This image was taken at an angle · the leg is involved · male patient, age 18–29: 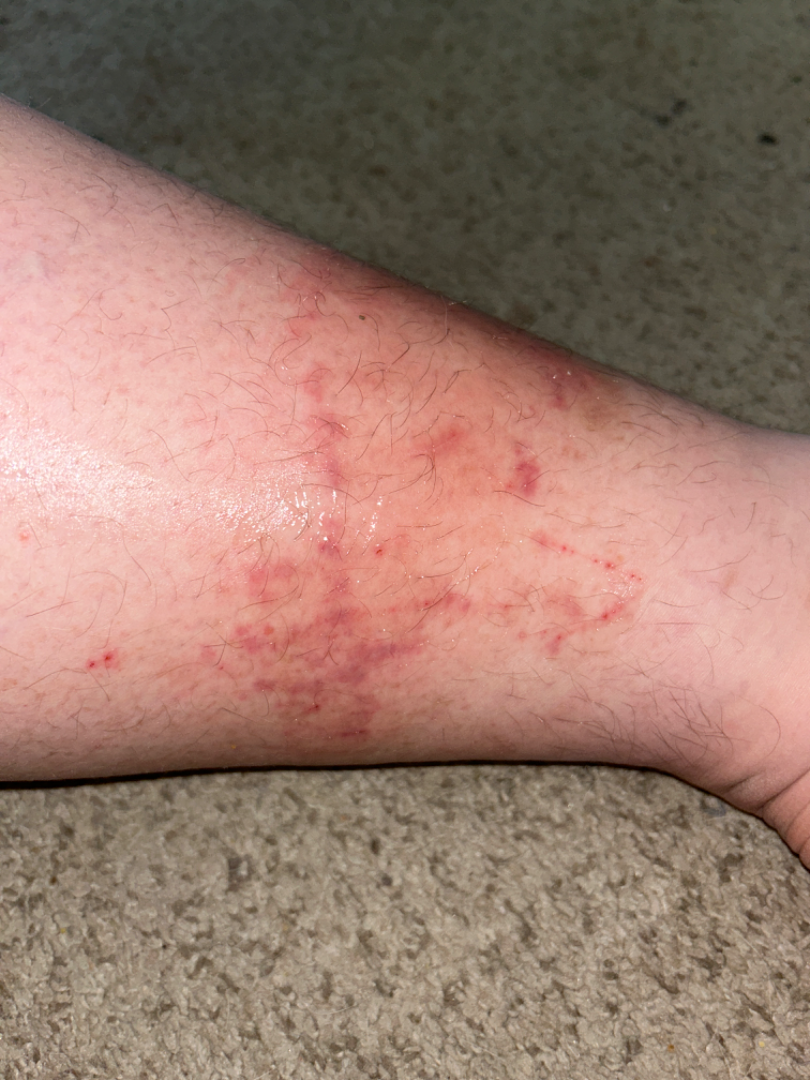| feature | finding |
|---|---|
| differential diagnosis | the impression on review was Allergic Contact Dermatitis |